A dermoscopy image of a single skin lesion.
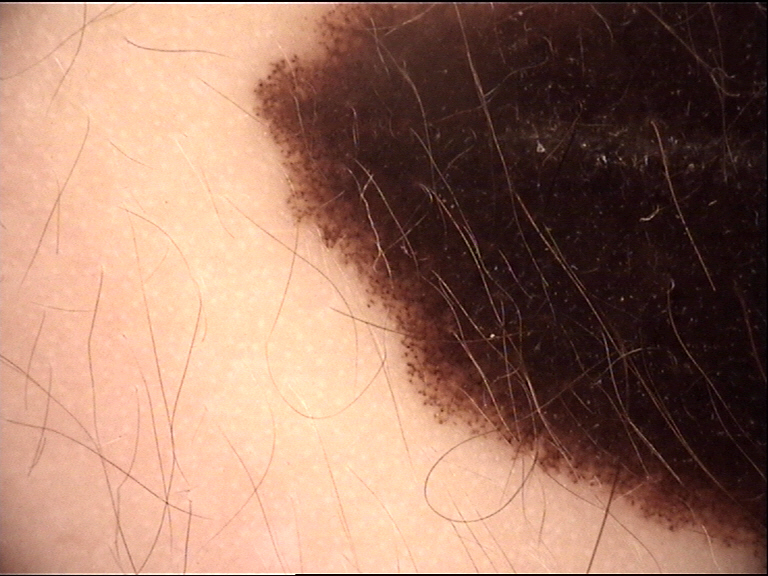label: congenital compound nevus (expert consensus).